A dermoscopic close-up of a skin lesion. A female patient aged around 15: 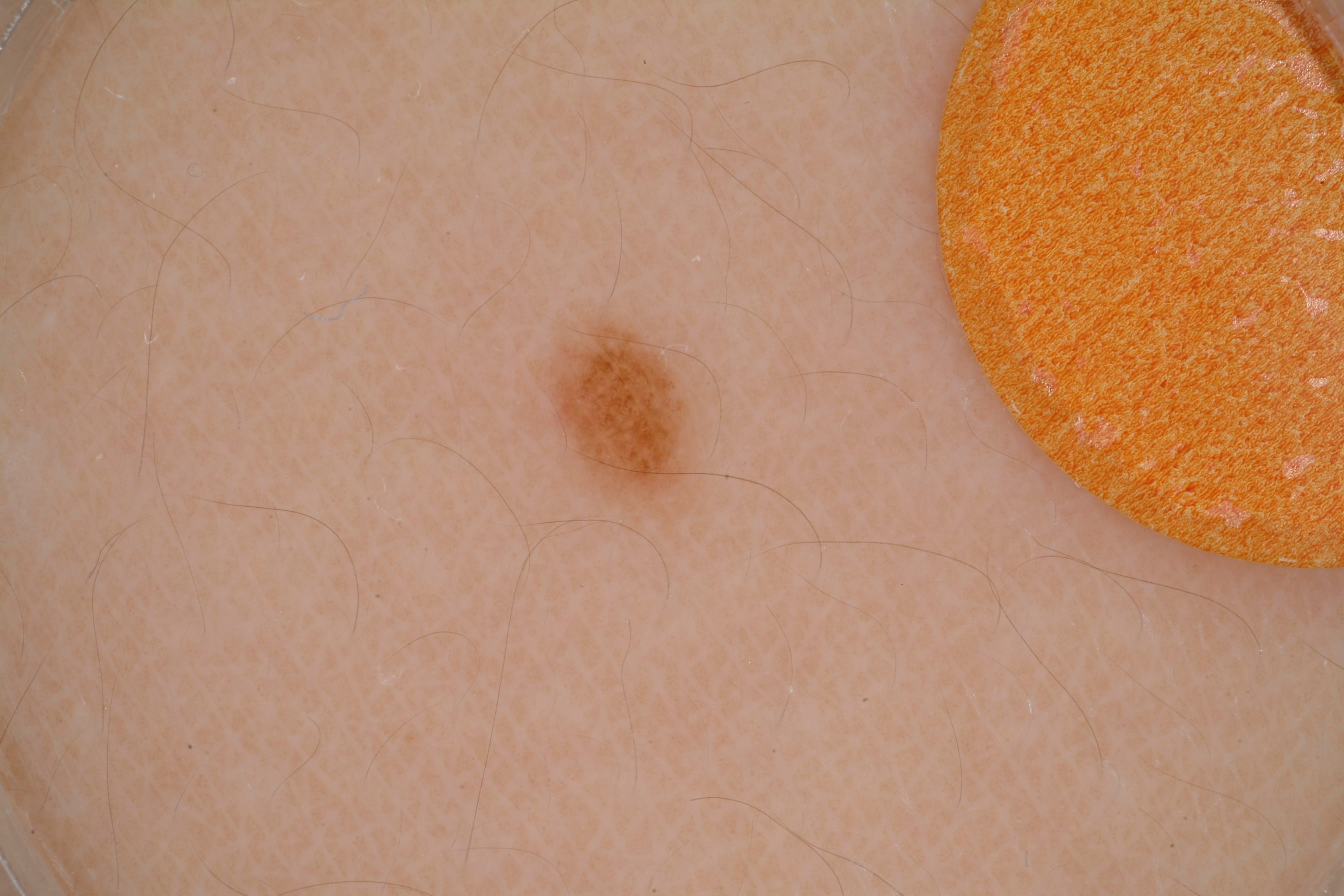On dermoscopy, the lesion shows no negative network, streaks, pigment network, or milia-like cysts. The lesion occupies the region left=508, top=288, right=715, bottom=509. The clinical diagnosis was a melanocytic nevus.